The patient reports associated fatigue. Self-categorized by the patient as a rash. The affected area is the back of the hand and top or side of the foot. The patient is 30–39, female. Reported lesion symptoms include itching, burning and pain. The patient reports the lesion is raised or bumpy and fluid-filled. Close-up view. The condition has been present for one to three months — 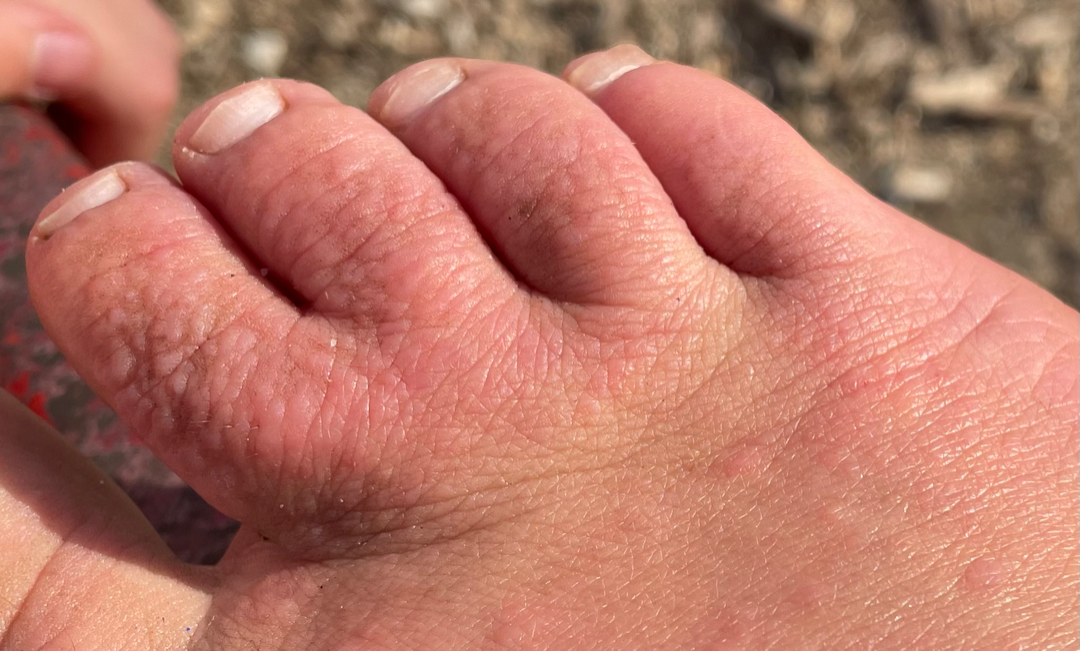assessment: unable to determine.